A dermoscopy image of a single skin lesion: 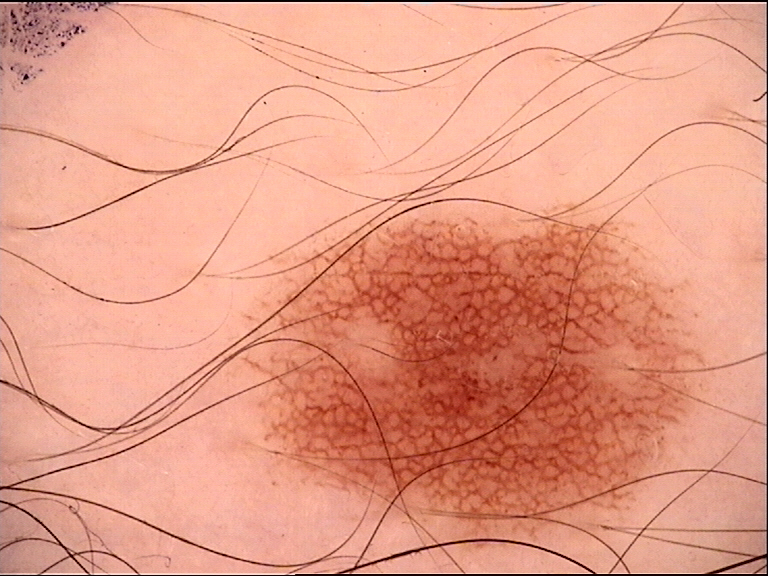Diagnosed as a junctional nevus.